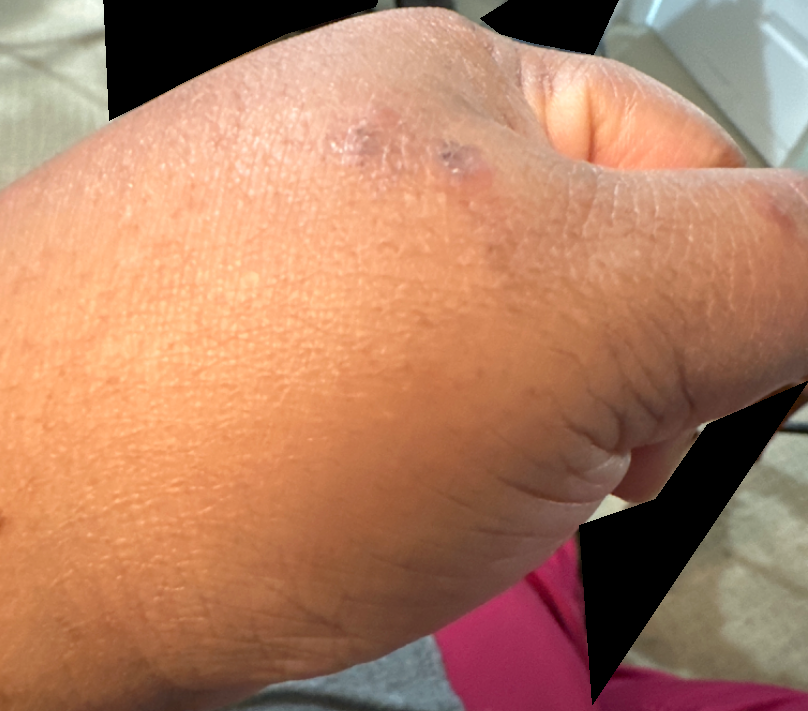assessment = indeterminate from the photograph.